A dermoscopy image of a single skin lesion.
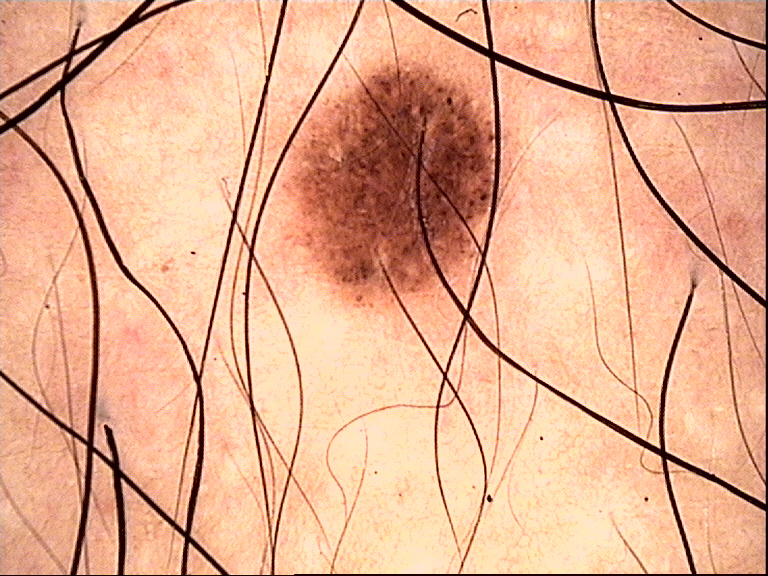Labeled as a benign lesion — a dysplastic junctional nevus.